Skin type II; a male patient in their 70s; history notes pesticide exposure and prior malignancy (patient or family): 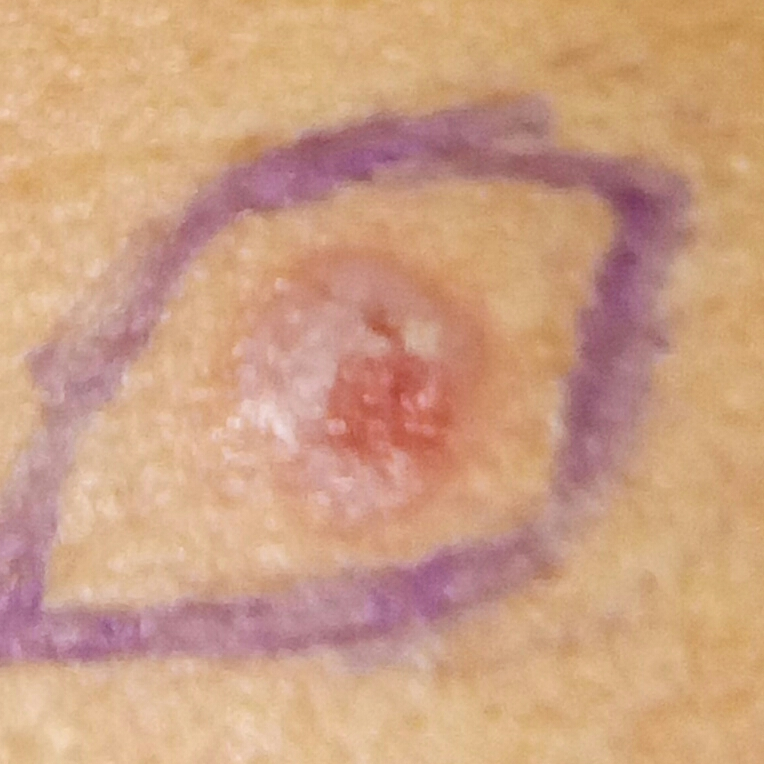Q: Where on the body is the lesion?
A: the back
Q: Any reported symptoms?
A: itching
Q: What is the diagnosis?
A: squamous cell carcinoma (biopsy-proven)